The lesion involves the back of the torso, head or neck, front of the torso, leg, back of the hand and top or side of the foot · an image taken at an angle — 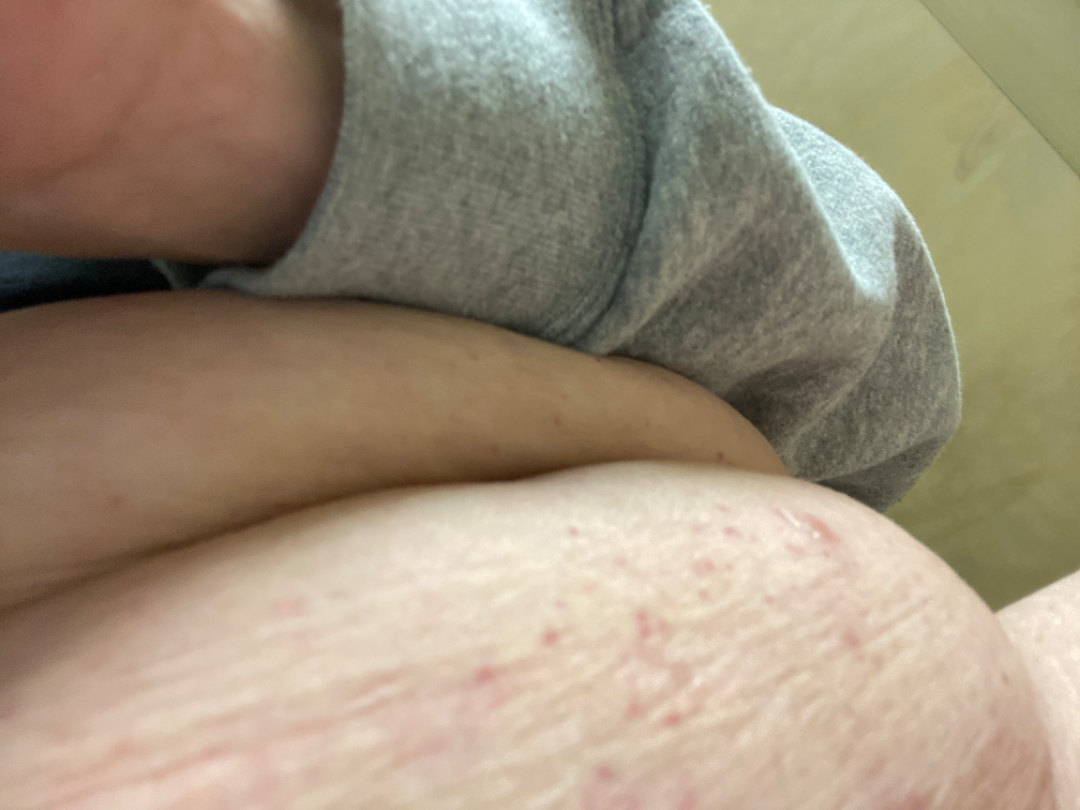Reported duration is less than one week.
Texture is reported as flat.
Self-categorized by the patient as a rash.
The reviewing clinician's impression was: Scabies, Eczema and Hypersensitivity were each considered, in no particular order.